A dermoscopic image of a skin lesion — 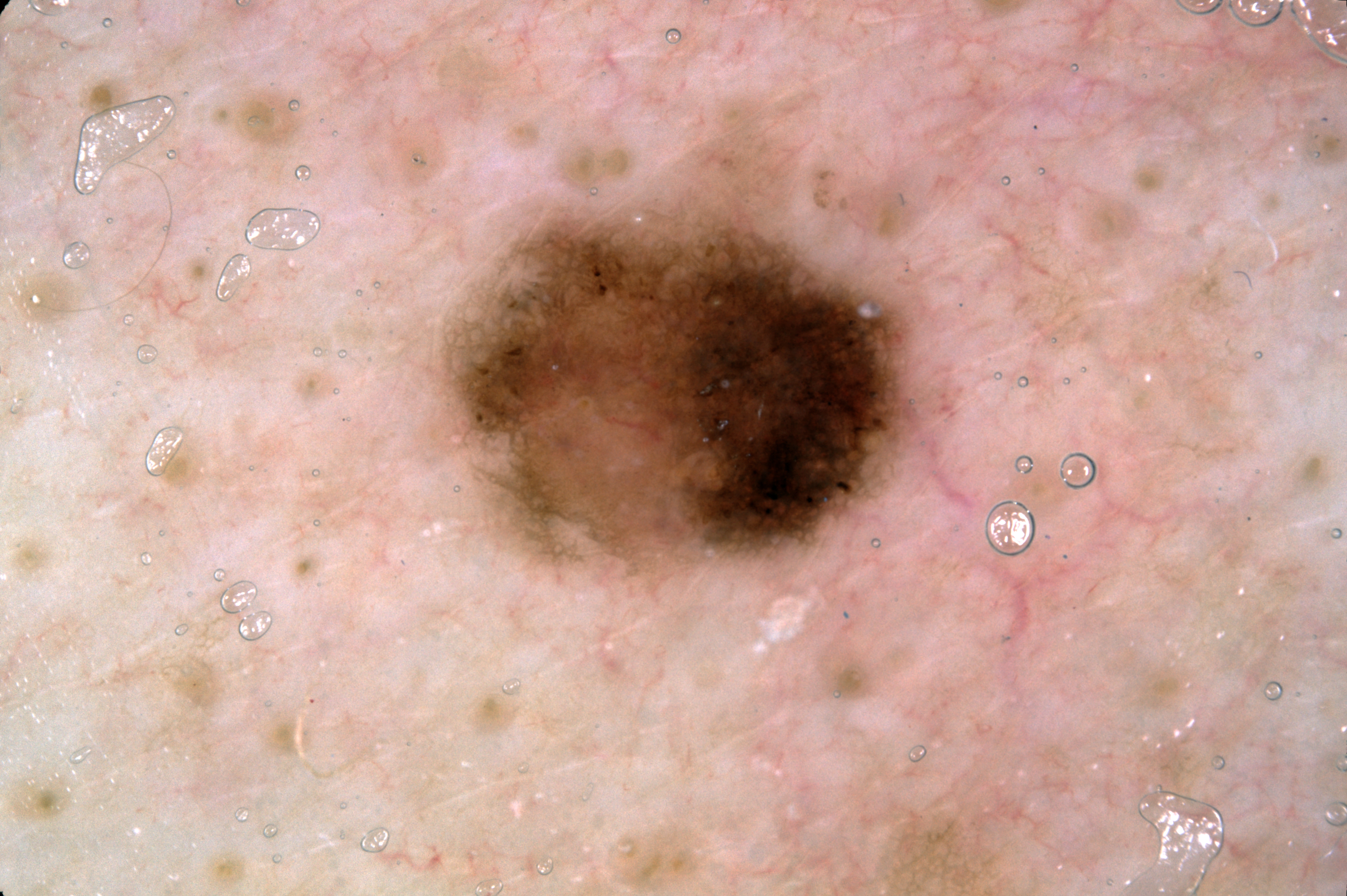Findings:
With coordinates (x1, y1, x2, y2), the lesion occupies the region box(442, 188, 923, 583). The lesion takes up a moderate portion of the field. Dermoscopic examination shows milia-like cysts and pigment network.
Impression:
The clinical diagnosis was a melanocytic nevus, a benign lesion.